A male patient age 62. The patient says their skin reddens with sun exposure. A clinical photograph of a skin lesion. The patient describes having few moles overall. Collected as part of a research study, without a referral diagnosis:
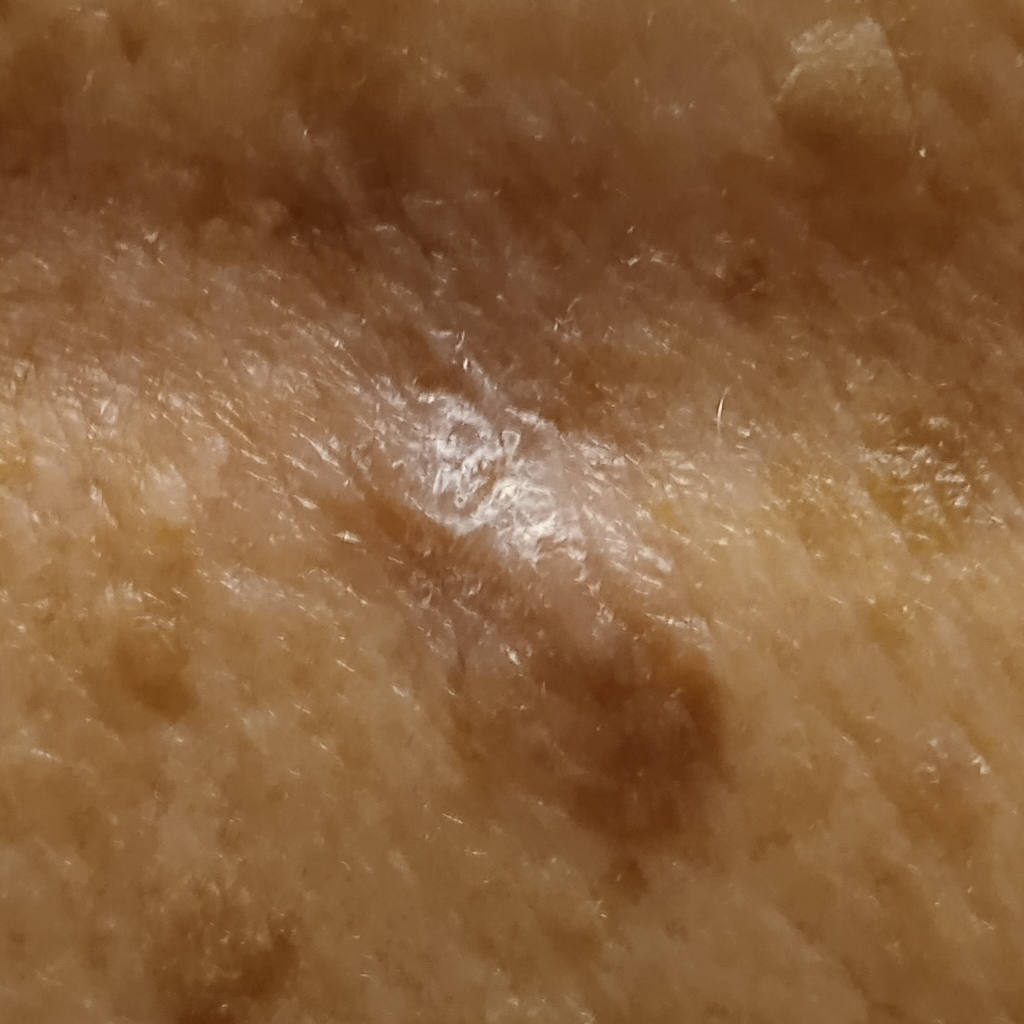Case summary: The lesion involves the back. The lesion measures approximately 13.8 mm. Assessment: The diagnostic impression was a squamous cell carcinoma.